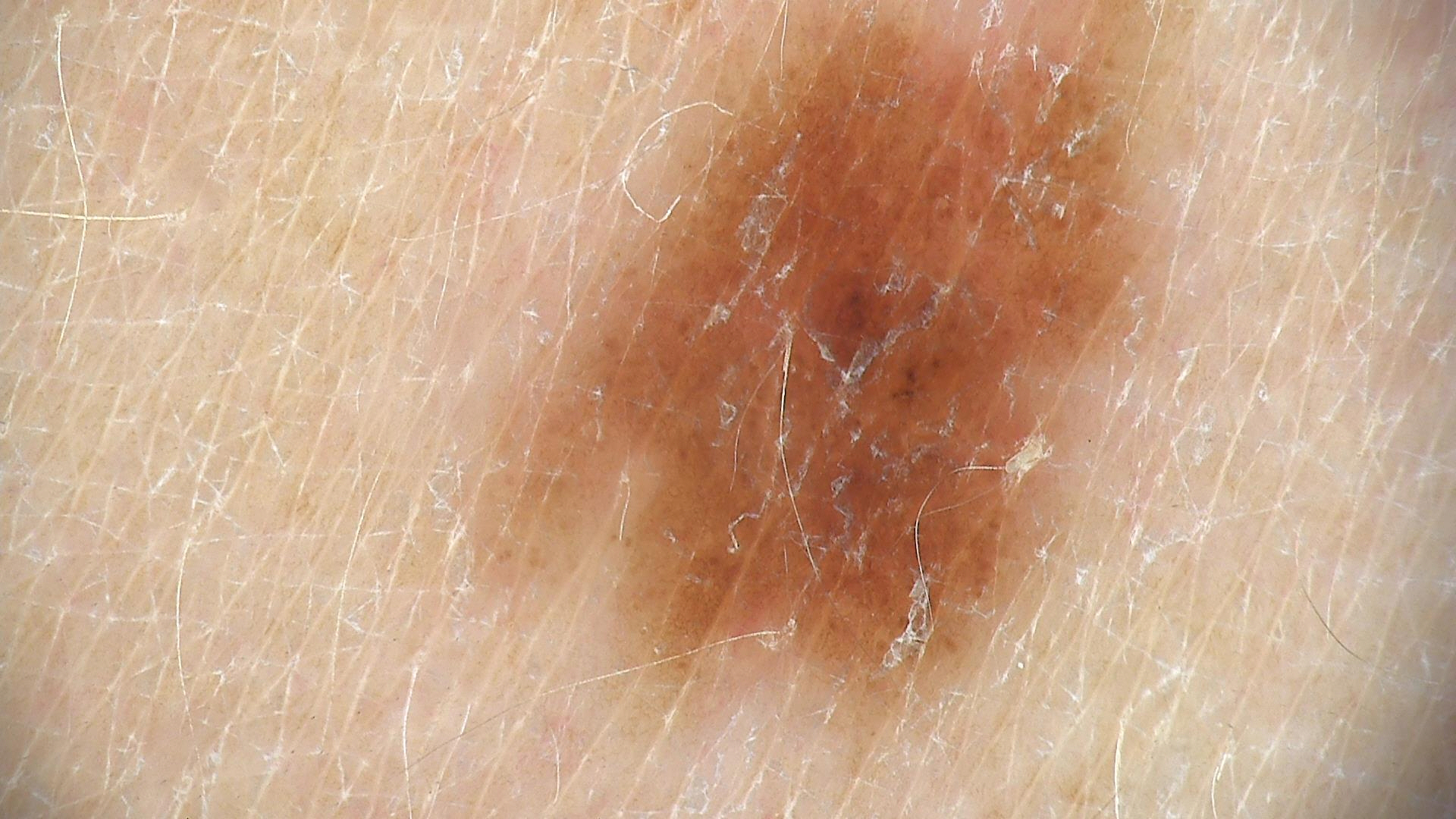class = dysplastic junctional nevus (expert consensus)